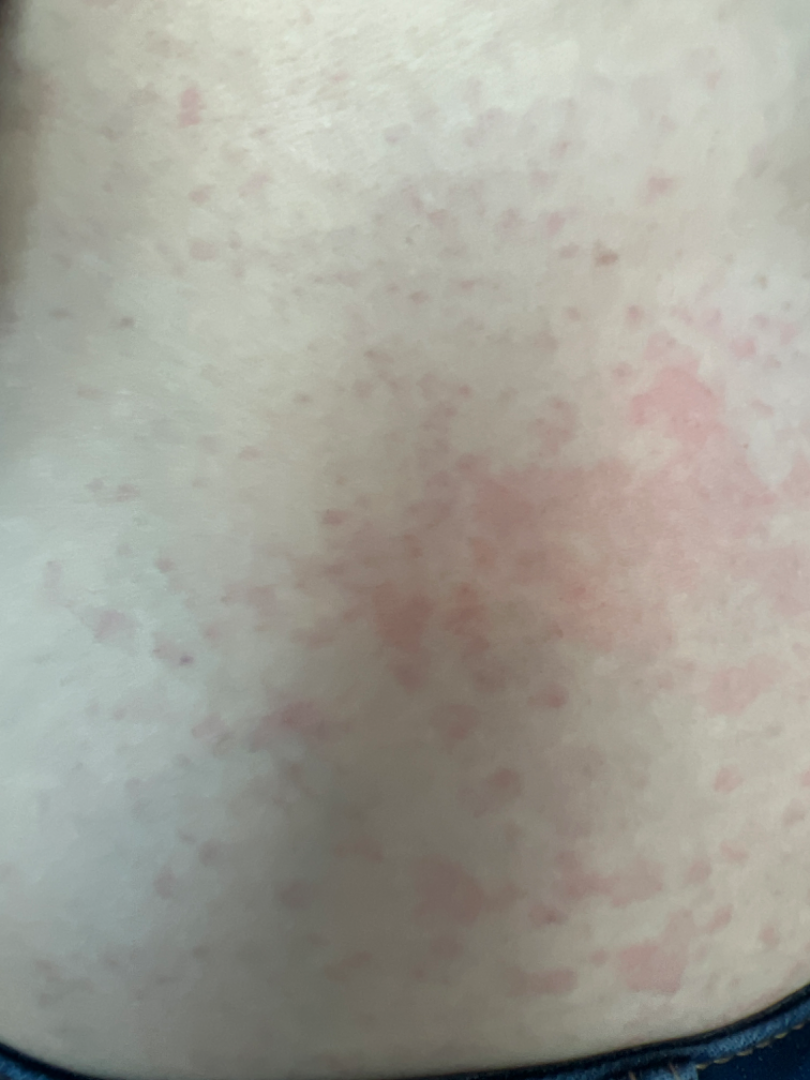Patient information: Reported duration is less than one week. FST I; lay graders estimated MST 1 (US pool) or 2 (India pool). Self-categorized by the patient as a rash. Located on the front of the torso, back of the torso and leg. Symptoms reported: itching, bothersome appearance and pain. Associated systemic symptoms include fatigue. The patient reports the lesion is raised or bumpy. A close-up photograph. Review: On photographic review, Hypersensitivity and Allergic Contact Dermatitis were considered with similar weight; a remote consideration is Viral Exanthem.